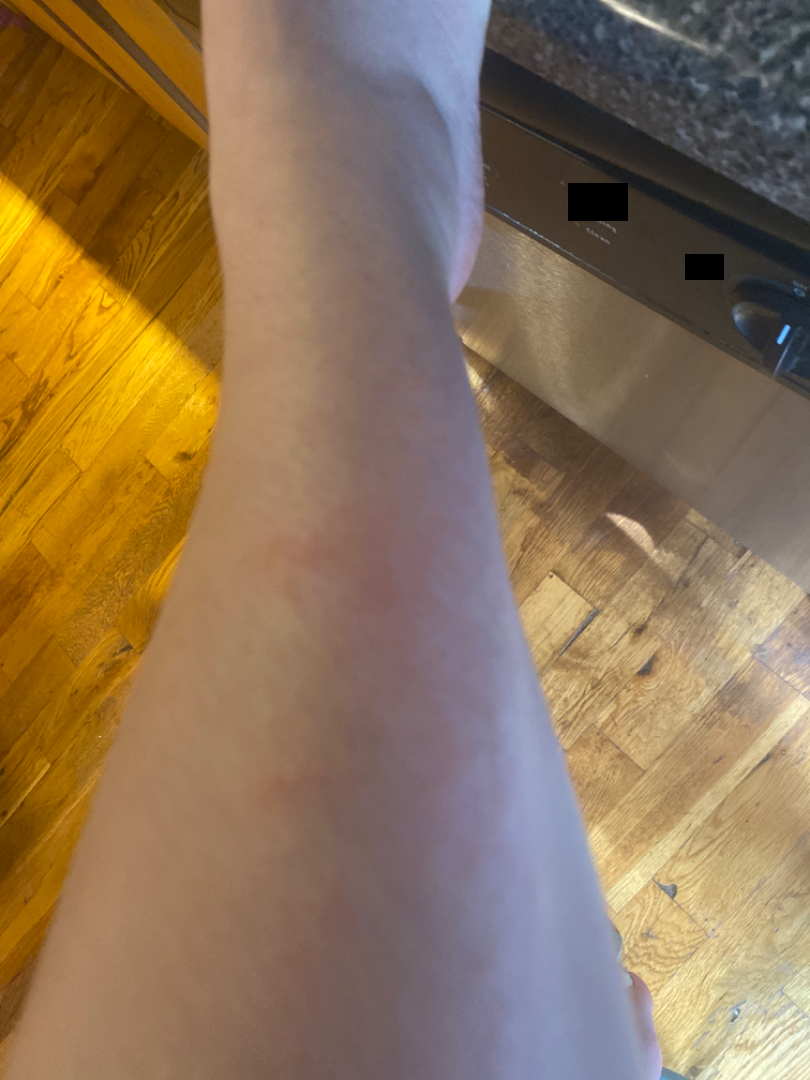<summary>
  <assessment>could not be assessed</assessment>
  <shot_type>at an angle</shot_type>
</summary>